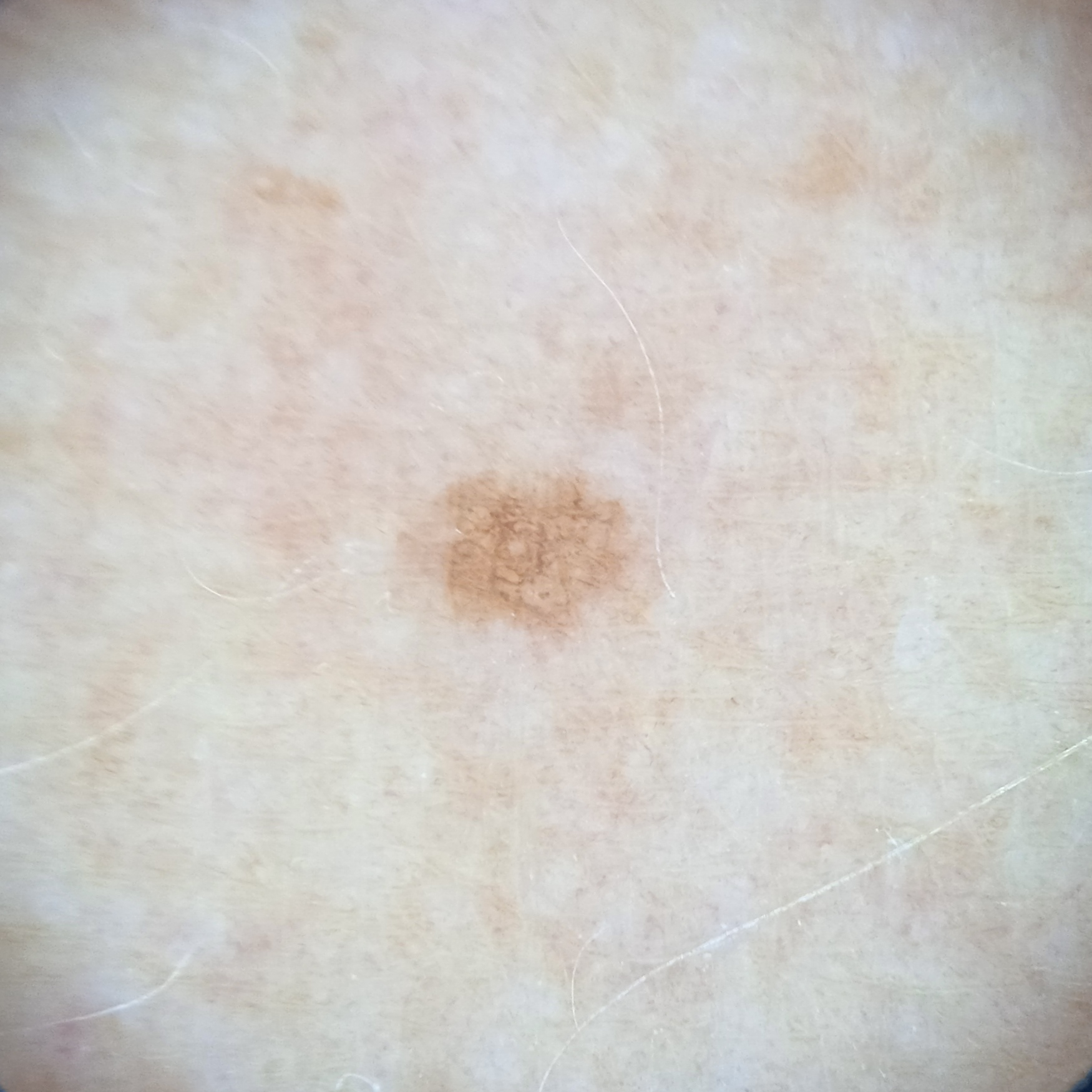modality: dermoscopic image
risk factors: a personal history of skin cancer
sun reaction: skin reddens with sun exposure
referral context: research study (no referral diagnosis)
subject: female, 67 years old
size: 2.3 mm
diagnostic label: melanocytic nevus (dermatologist consensus)